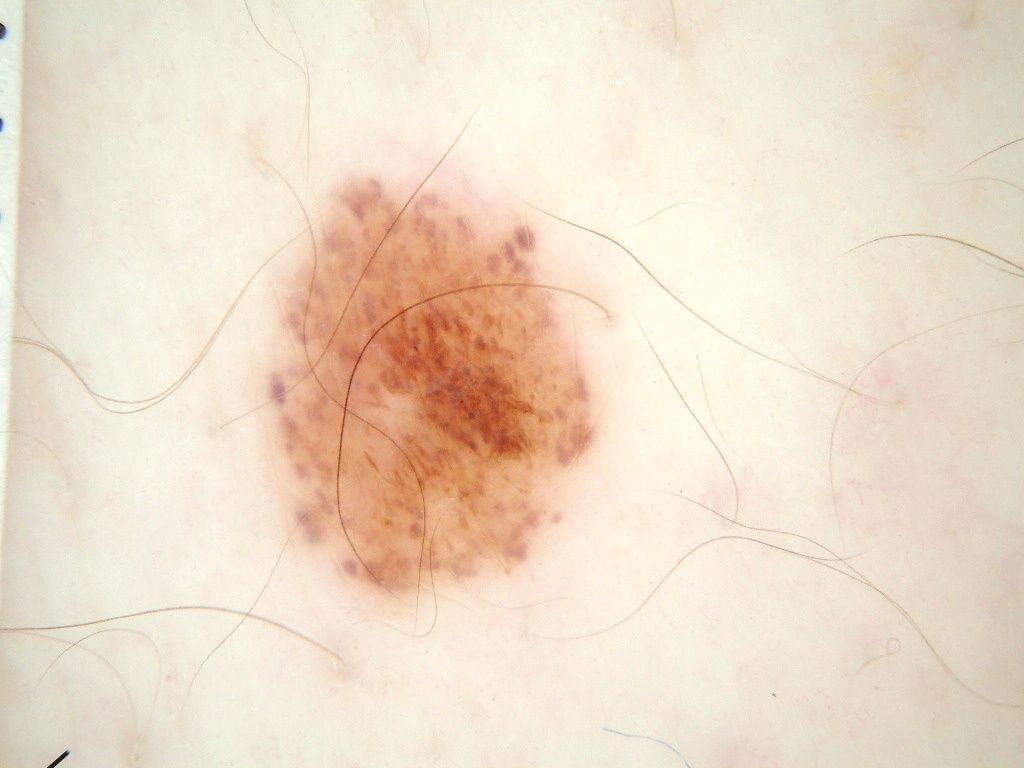<dermoscopy>
  <image>
    <modality>dermoscopy</modality>
  </image>
  <dermoscopic_features>
    <present>globules</present>
    <absent>streaks</absent>
  </dermoscopic_features>
  <lesion_location>
    <bbox_xyxy>262, 176, 597, 604</bbox_xyxy>
  </lesion_location>
  <lesion_extent>
    <approx_field_fraction_pct>13</approx_field_fraction_pct>
  </lesion_extent>
  <diagnosis>
    <malignancy>benign</malignancy>
    <provenance>clinical</provenance>
  </diagnosis>
</dermoscopy>